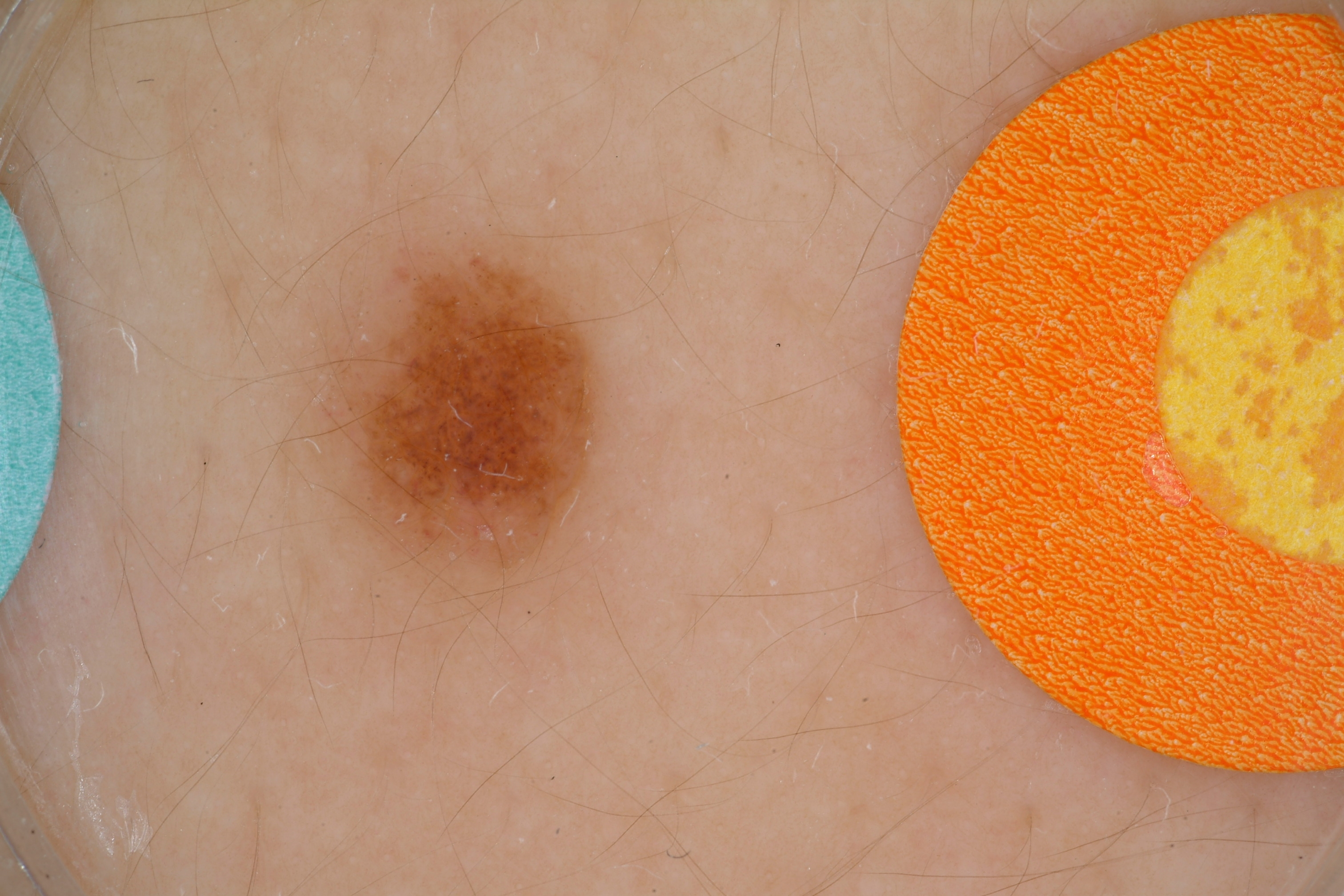Findings:
* image — dermoscopy of a skin lesion
* lesion location — x1=317, y1=232, x2=606, y2=607
* absent dermoscopic features — globules and streaks
* diagnosis — a benign skin lesion